The lesion involves the leg; male patient, age 18–29; the photo was captured at an angle: 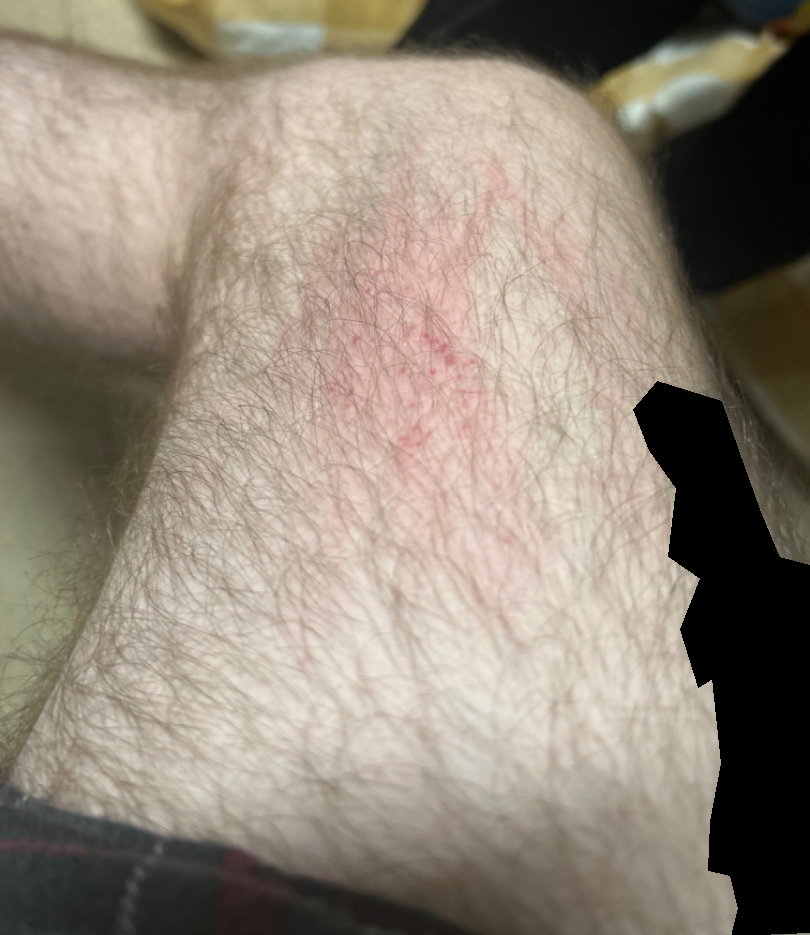No differential diagnosis could be assigned on photographic review.